A female patient aged approximately 30. A dermatoscopic image of a skin lesion.
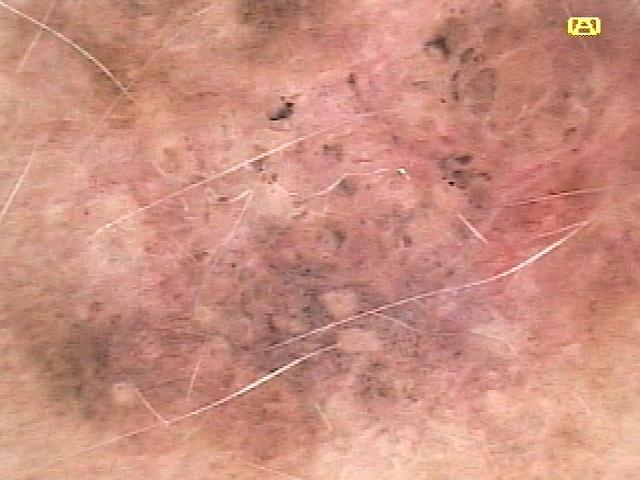• body site: the trunk
• pathology: Nevus (biopsy-proven)